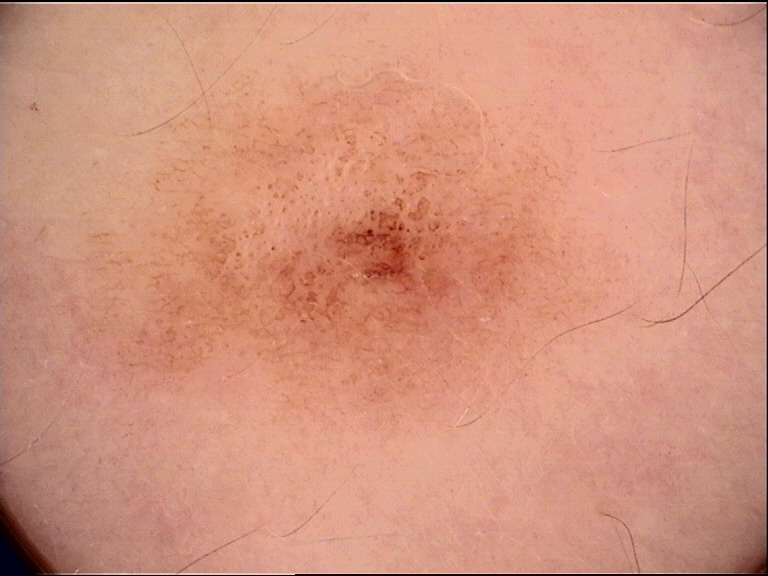The diagnostic label was a dysplastic junctional nevus.